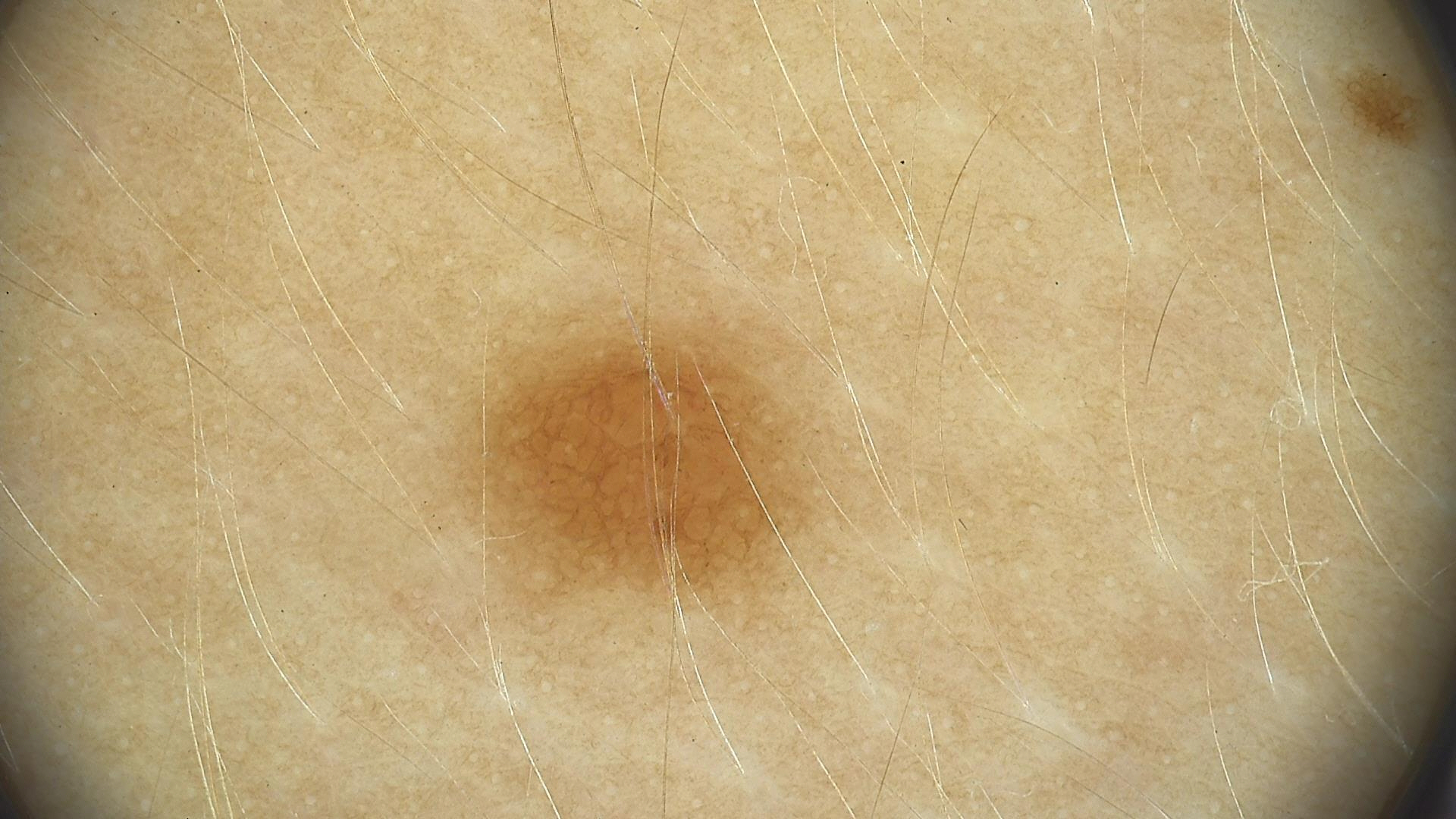– class · dysplastic junctional nevus (expert consensus)